Symptoms reported: itching · the affected area is the arm, leg and front of the torso · the subject is a female aged 18–29 · the lesion is described as fluid-filled · the photograph is a close-up of the affected area · no relevant systemic symptoms · present for one to four weeks:
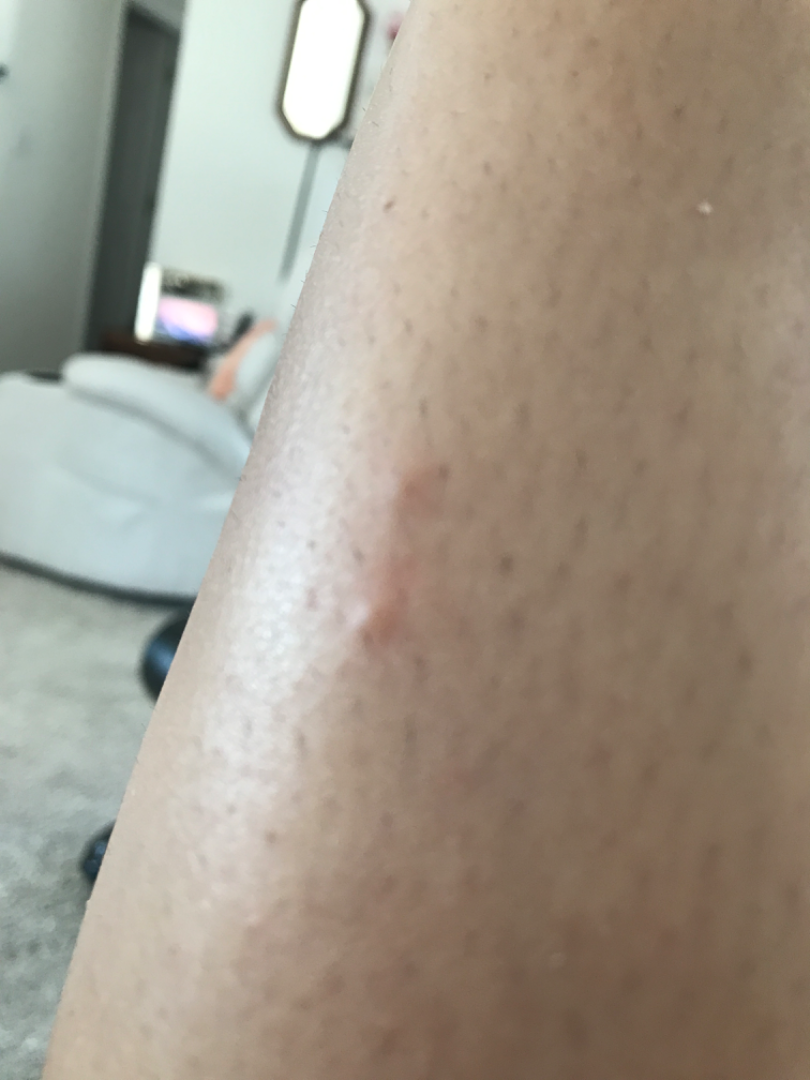Assessment:
Eczema (weight 0.67); Scabies (weight 0.33).